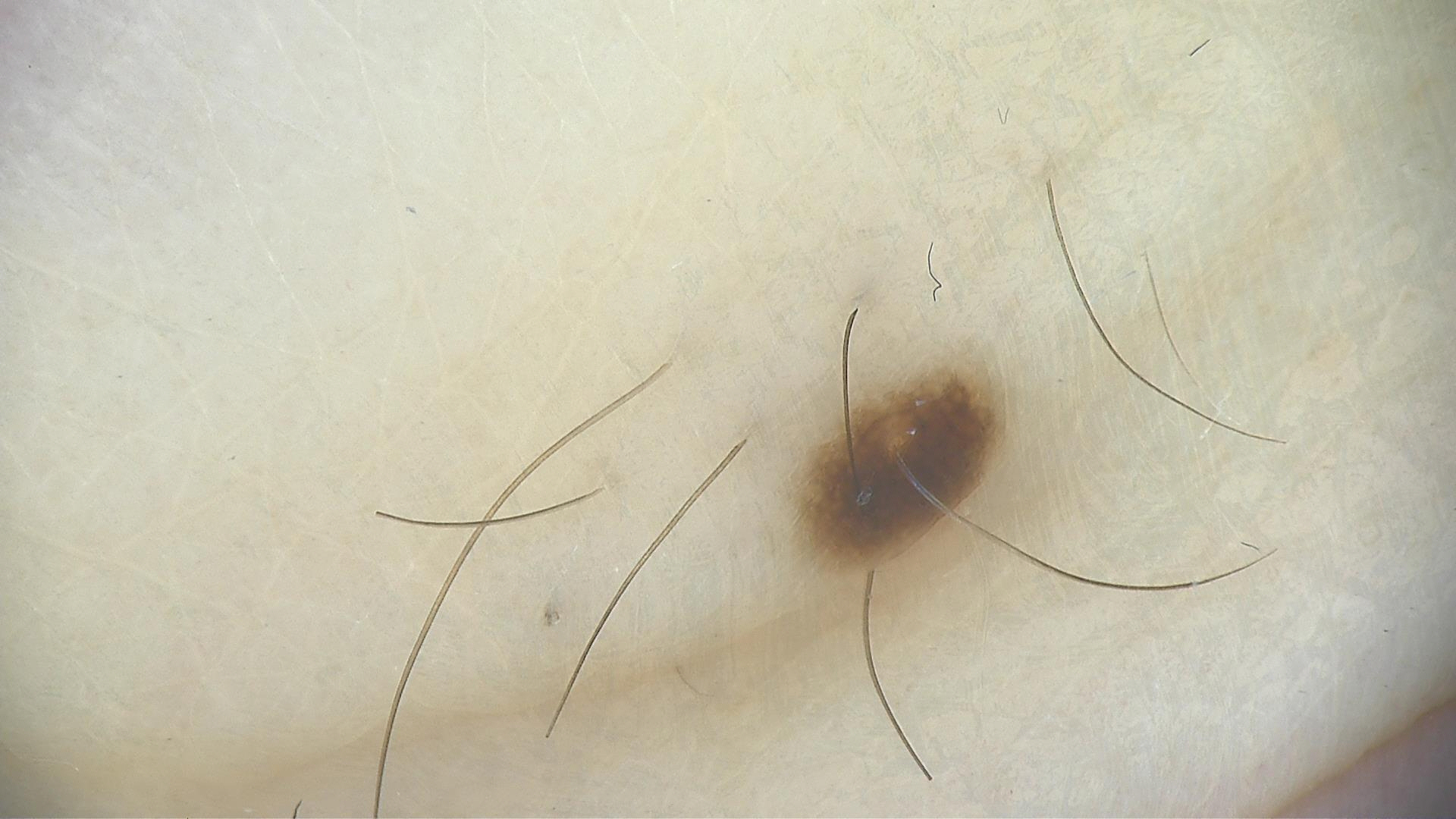class: compound nevus (expert consensus).